A clinical photograph of a skin lesion · the referring clinician suspected basal cell carcinoma · few moles overall by the patient's own estimate · a male subject 67 years of age · the patient reports a personal history of skin cancer, no prior organ transplant, and no sunbed use · the patient says their skin tans without first burning: 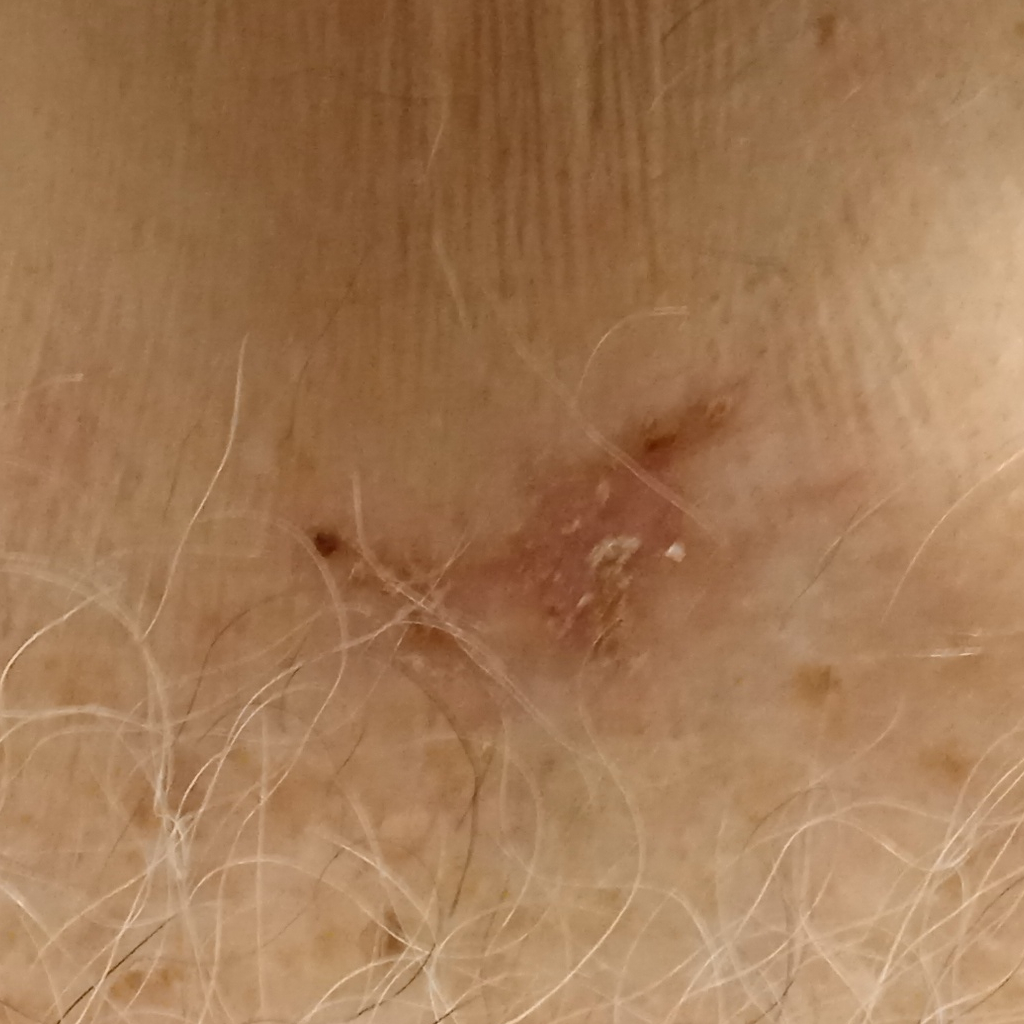Located on the torso.
The lesion measures approximately 19 mm.
Histopathologically confirmed as a basal cell carcinoma, following a punch biopsy, with tumor thickness 0.8 mm.